The patient notes the lesion is rough or flaky · this image was taken at an angle · reported duration is three to twelve months · the patient described the issue as a rash — 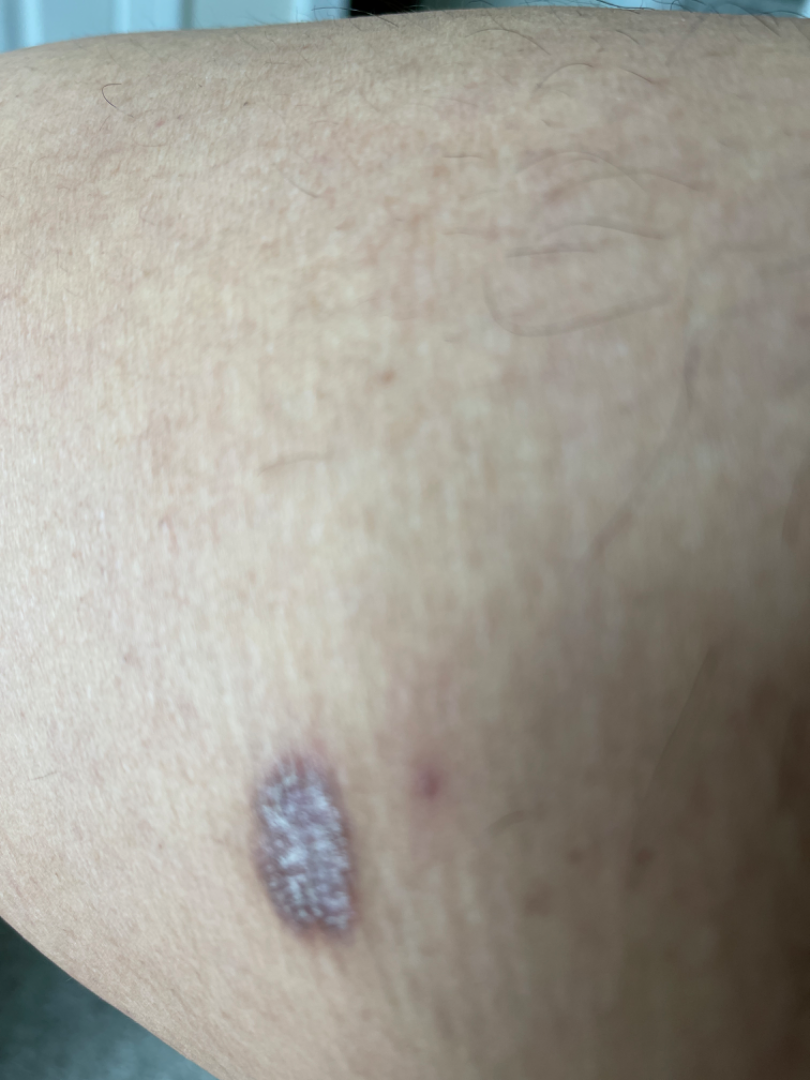differential:
  tied_lead:
    - Dermatofibroma
    - SK/ISK
  unlikely:
    - Melanoma